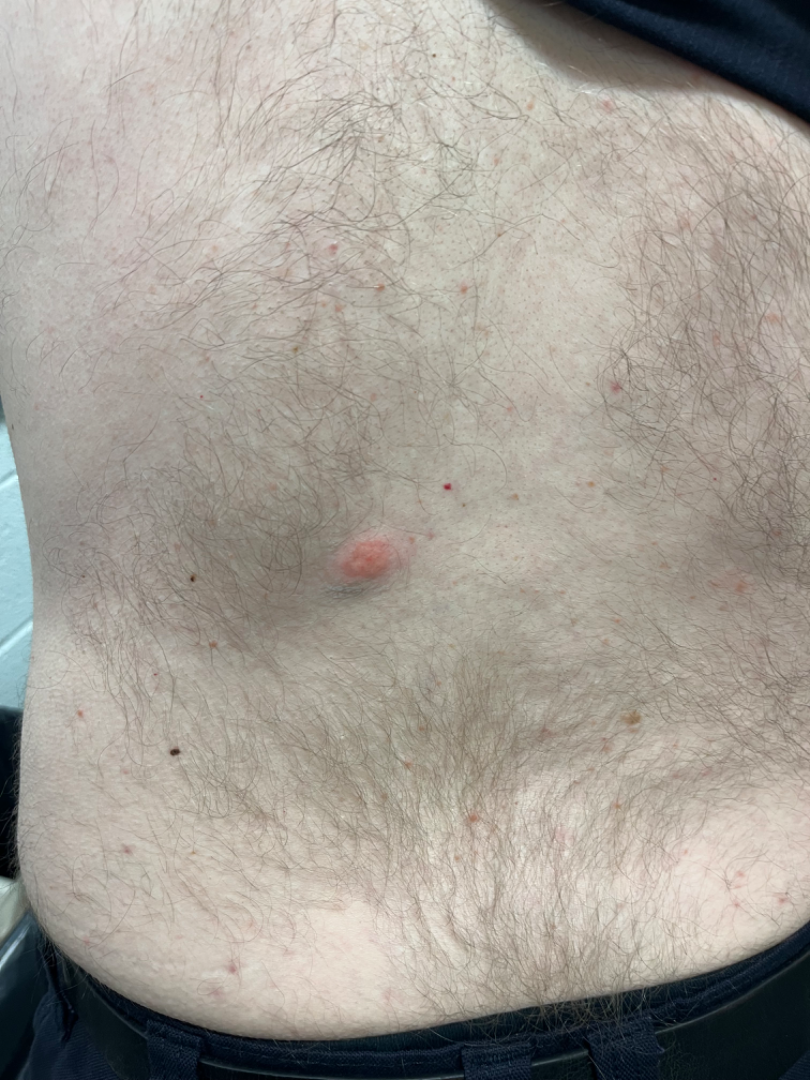<summary>
  <assessment>indeterminate from the photograph</assessment>
  <patient>male, age 50–59</patient>
  <shot_type>at a distance</shot_type>
  <skin_tone>
    <fitzpatrick>III</fitzpatrick>
    <fitzpatrick_source>self_reported</fitzpatrick_source>
    <monk_skin_tone>2, 4</monk_skin_tone>
  </skin_tone>
  <body_site>back of the torso</body_site>
  <patient_category>a rash</patient_category>
</summary>